Fitzpatrick III. The condition has been present for one to four weeks. The lesion involves the top or side of the foot. Texture is reported as fluid-filled and raised or bumpy. Symptoms reported: pain, itching, bothersome appearance, bleeding and enlargement. An image taken at a distance. The patient considered this a rash — 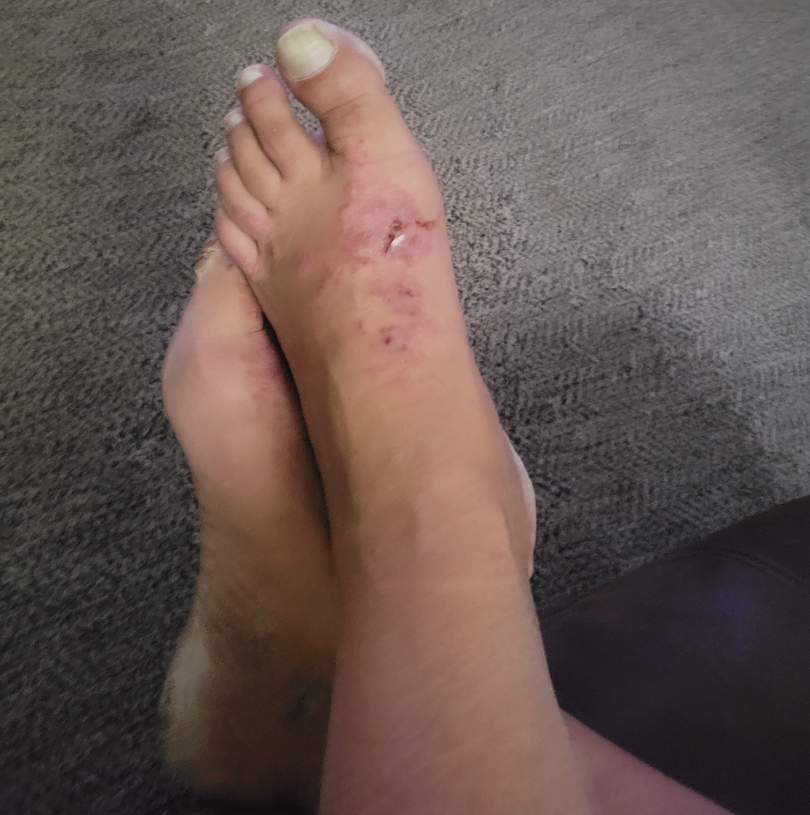Tinea (favored); Eczema (possible); Psoriasis (possible).